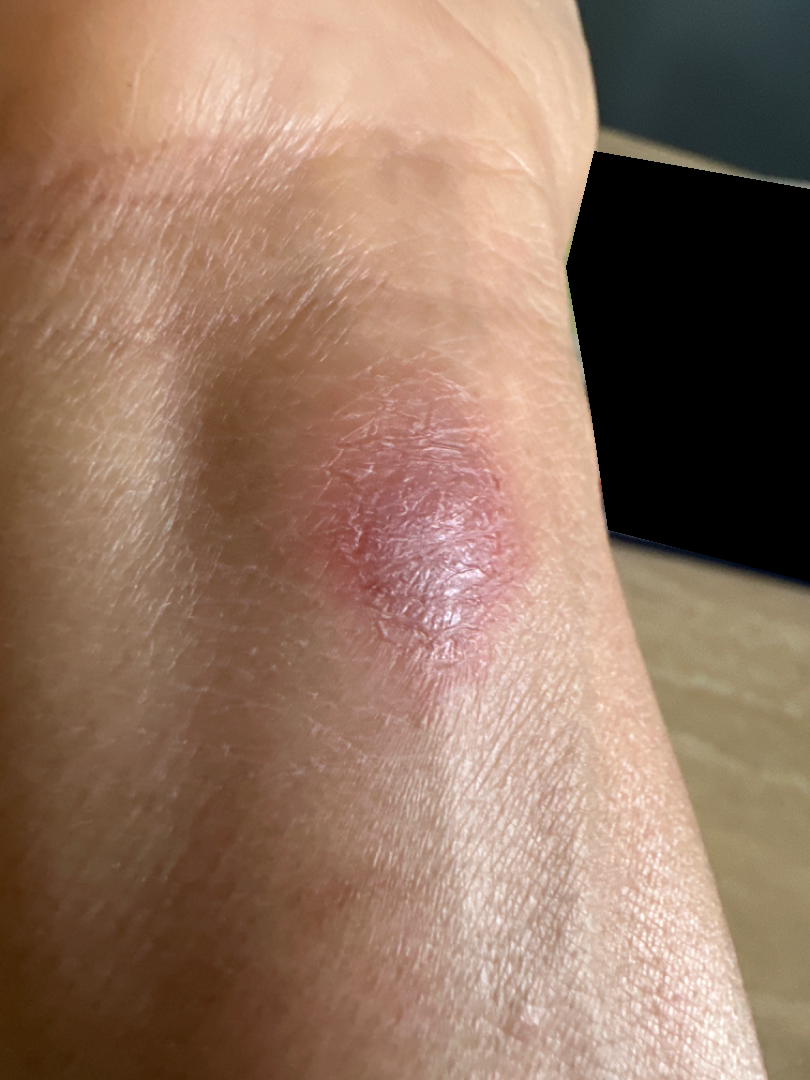Clinical context: The photo was captured at an angle. The condition has been present for one to four weeks. Symptoms reported: itching, burning and enlargement. Female contributor, age 50–59. The lesion is described as rough or flaky. Located on the arm. Skin tone: Fitzpatrick skin type IV. Assessment: On photographic review: the leading consideration is Allergic Contact Dermatitis; less probable is Abscess; lower on the differential is Cyst; less likely is Eczema; a more distant consideration is Acute and chronic dermatitis; a remote consideration is Irritant Contact Dermatitis.